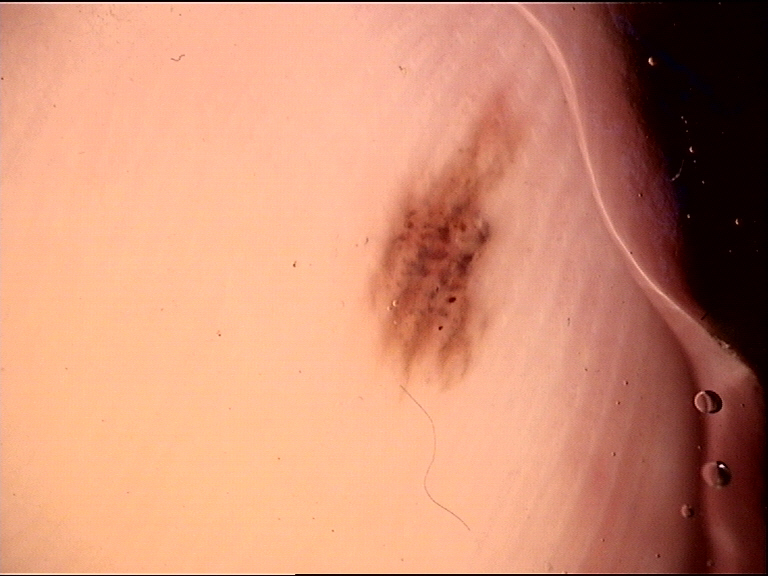Summary: A dermoscopy image of a single skin lesion. Conclusion: Labeled as a benign lesion — an acral dysplastic junctional nevus.